The patient indicates the lesion is flat. This is a close-up image. Fitzpatrick phototype II; lay reviewers estimated MST 3 — 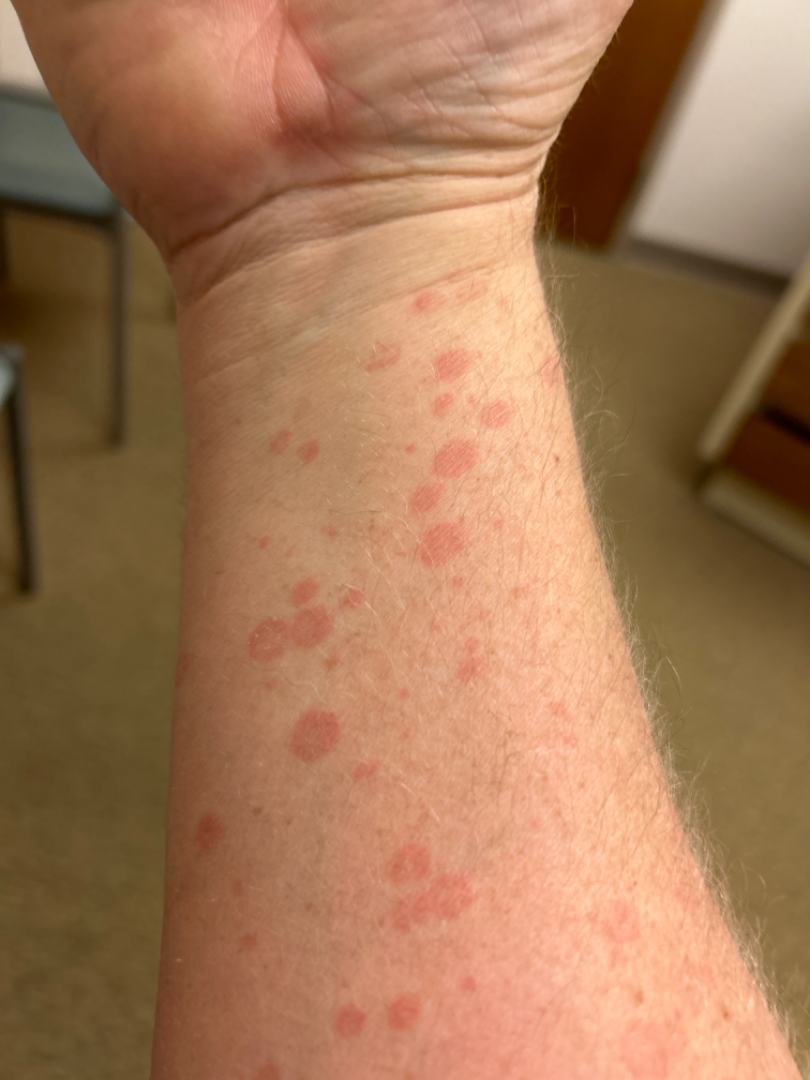| key | value |
|---|---|
| assessment | a single dermatologist reviewed the case: consistent with Tinea Versicolor |